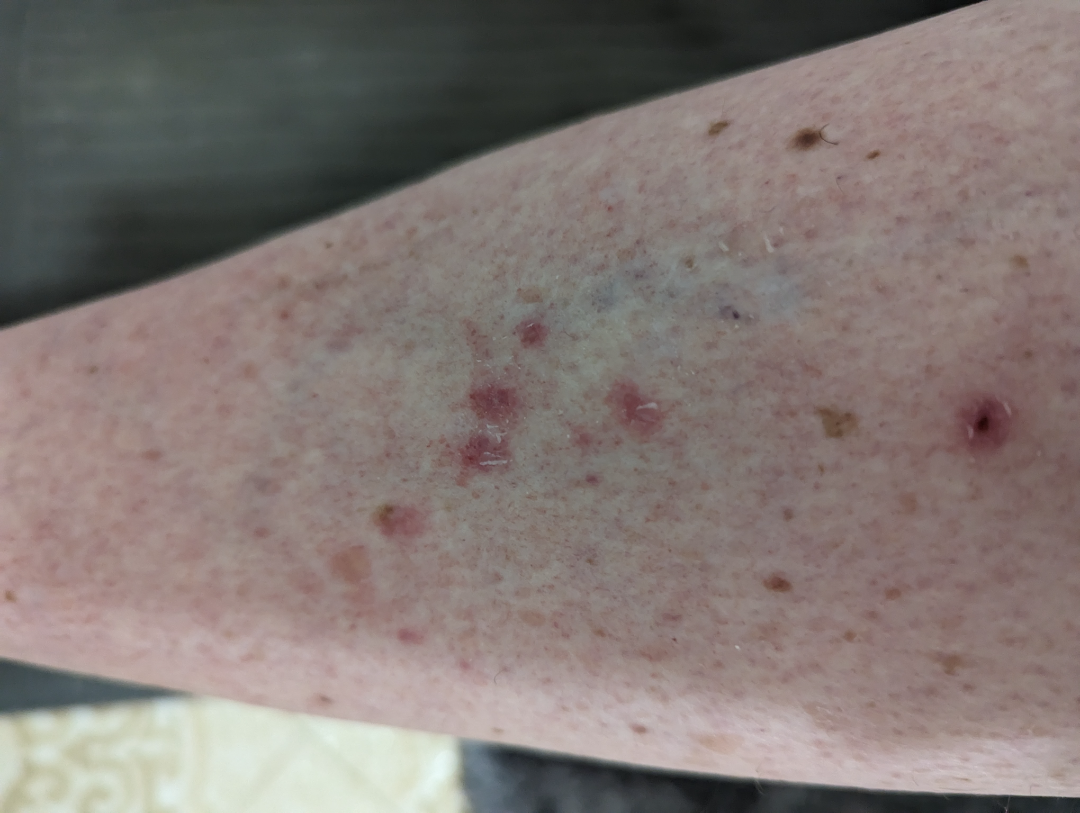The reviewing dermatologist's impression was: Pigmented purpuric eruption, Stasis Dermatitis and Eczema were considered with similar weight.